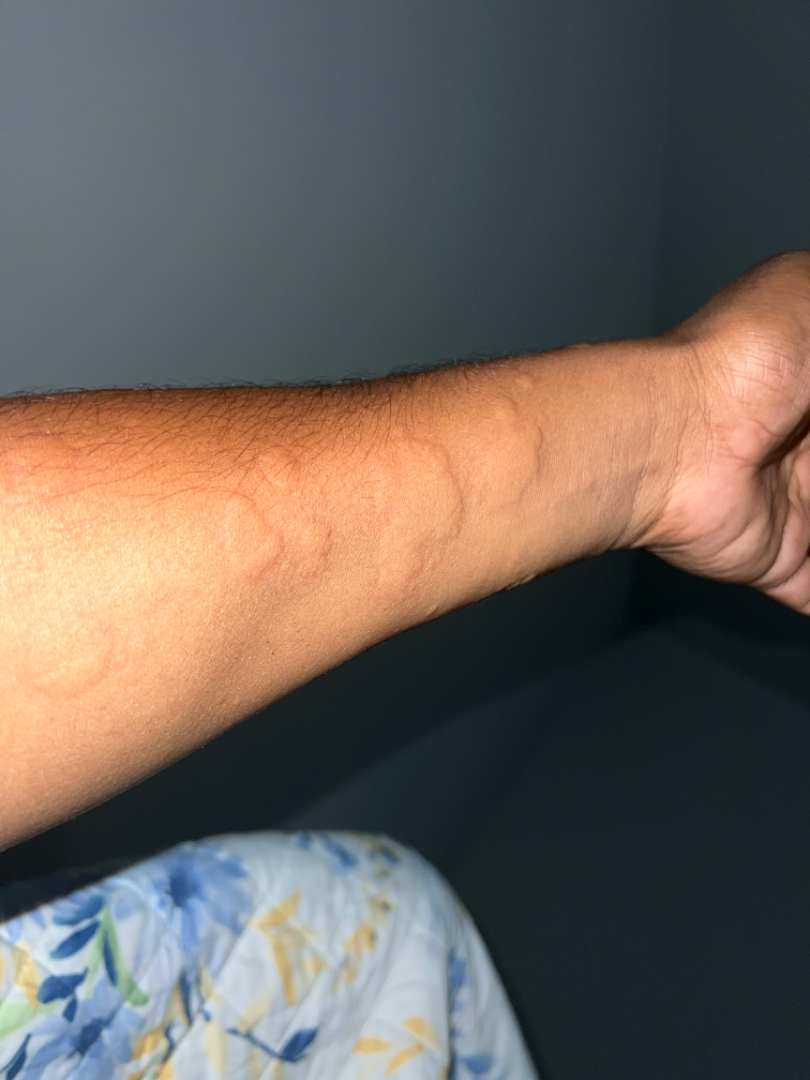The photograph was taken at a distance. Skin tone: Fitzpatrick skin type IV; lay reviewers estimated Monk skin tone scale 4 or 5. The reviewing dermatologist's impression was: the favored diagnosis is Urticaria.